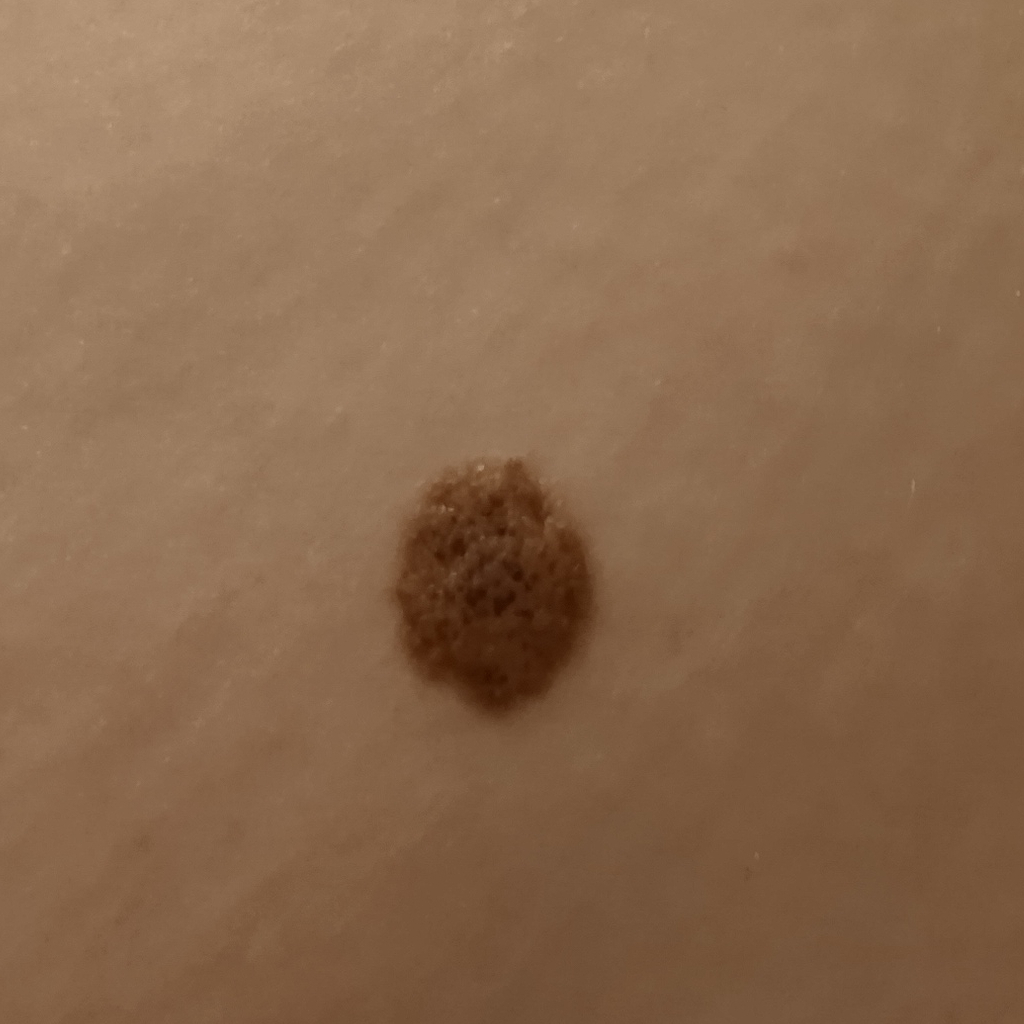The patient describes having numerous moles.
On a questionnaire the patient reported a history of sunbed use.
A female patient 26 years old.
The patient says their skin reddens with sun exposure.
Located on the torso.
The lesion measures approximately 12.1 mm.
Dermatologist review favored a melanocytic nevus.